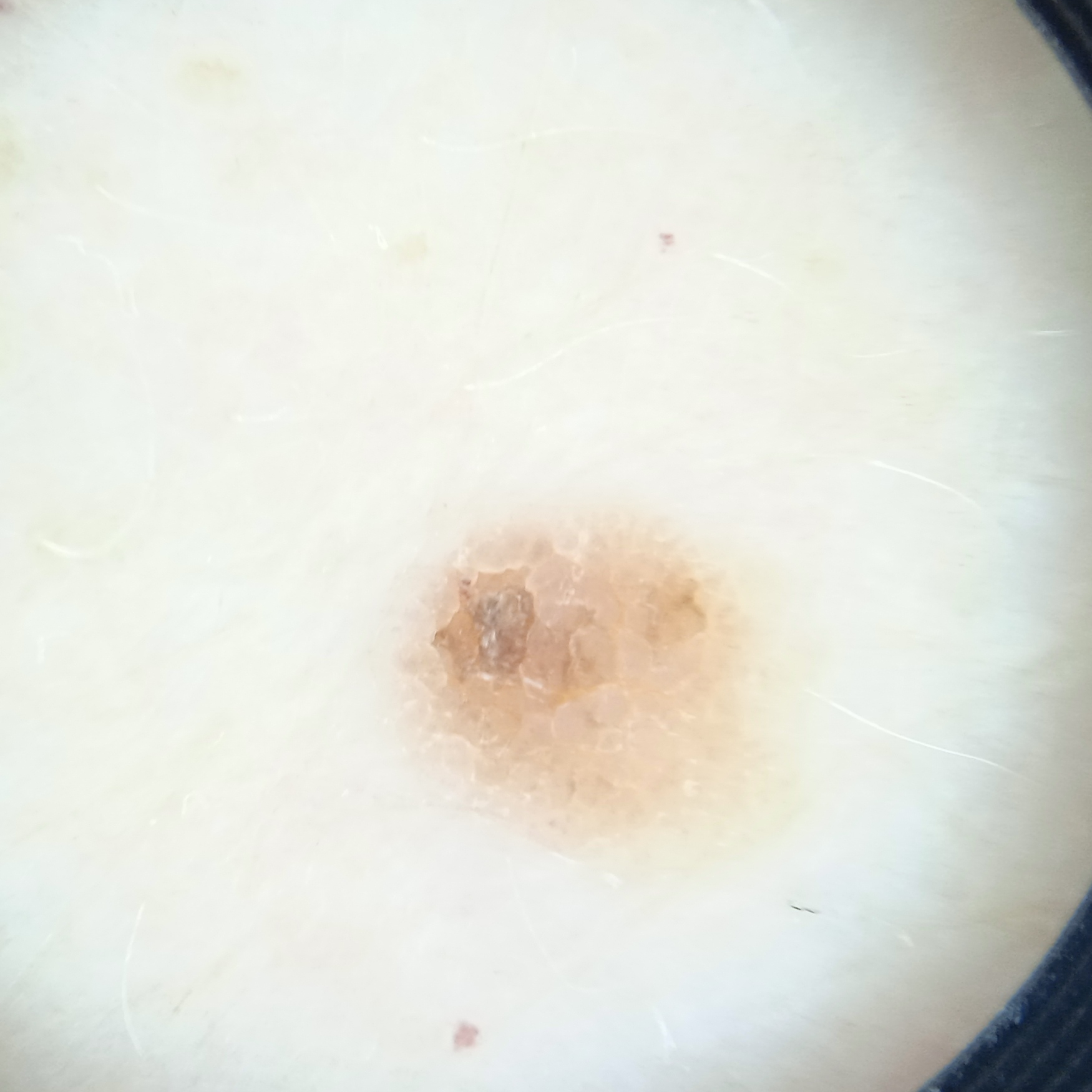imaging = dermatoscopic image; clinical context = research study (no referral diagnosis); body site = the torso; assessment = seborrheic keratosis (dermatologist consensus).